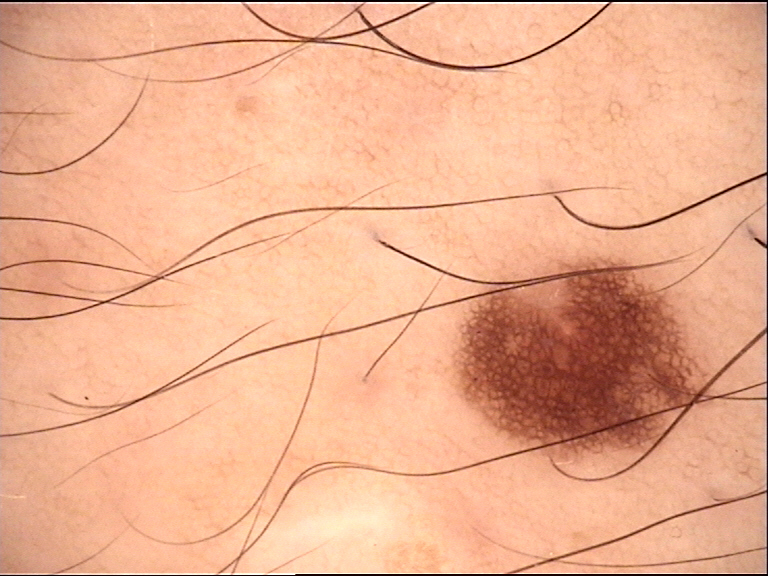Q: What is the imaging modality?
A: dermoscopy
Q: How is the lesion classified?
A: banal
Q: What was the diagnostic impression?
A: junctional nevus (expert consensus)